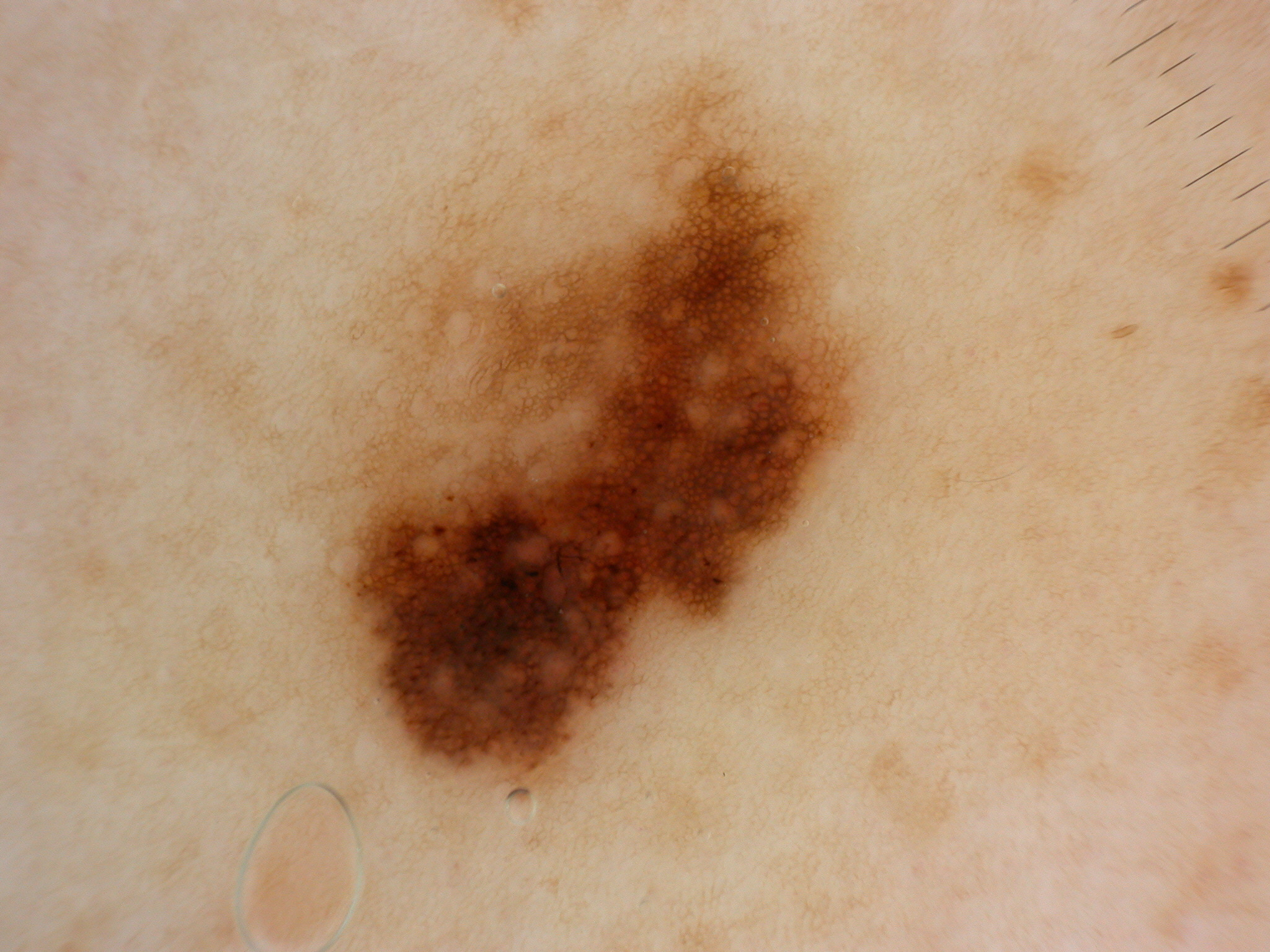Dermoscopy of a skin lesion. The lesion is bounded by x1=316 y1=88 x2=868 y2=801. A moderately sized lesion. The dermoscopic pattern shows globules and pigment network. The diagnostic assessment was a melanocytic nevus, a benign skin lesion.